A dermoscopy image of a single skin lesion:
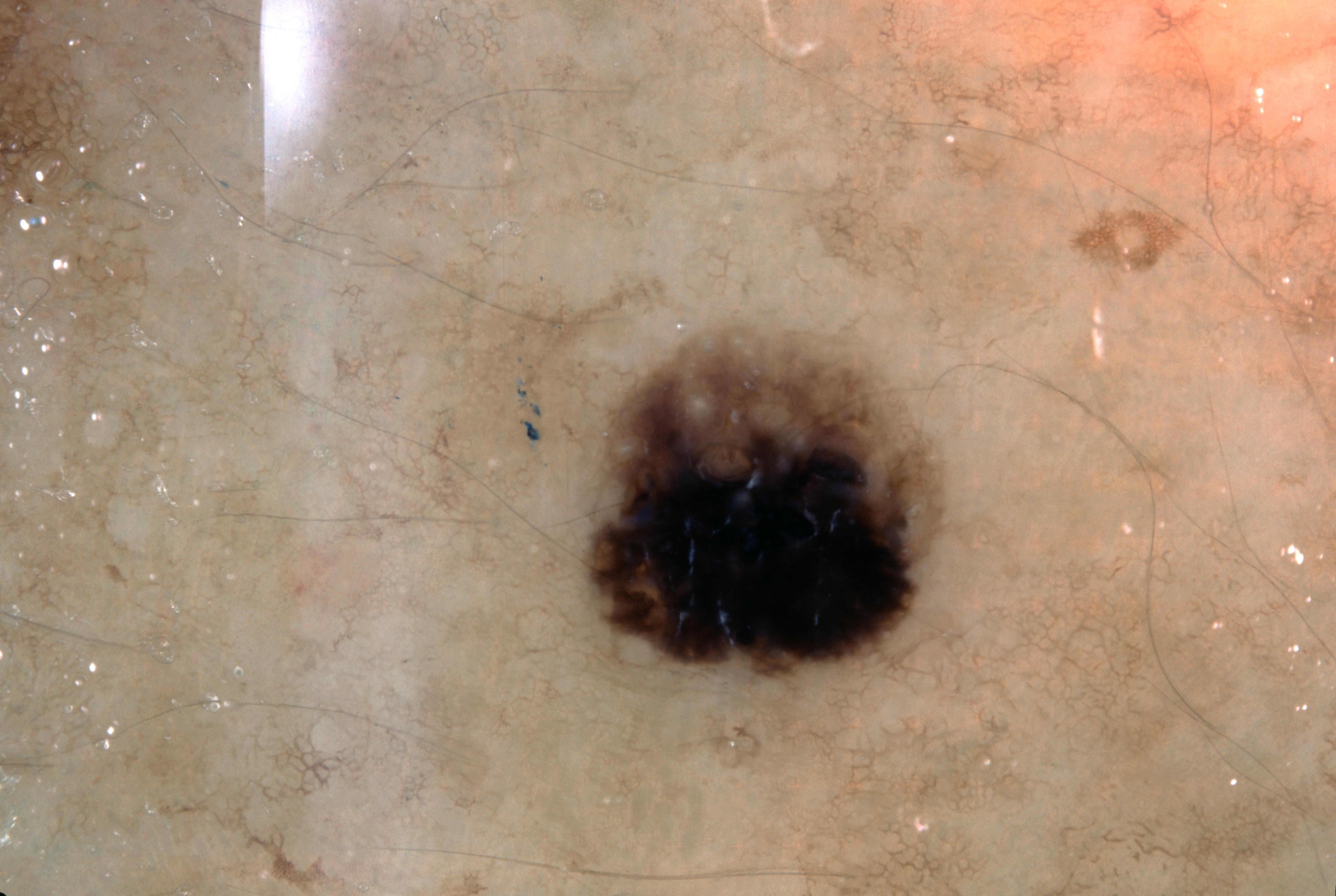Image and clinical context: In (x1, y1, x2, y2) order, the lesion occupies the region <bbox>585, 336, 939, 686</bbox>. The lesion takes up a moderate portion of the field. Dermoscopically, the lesion shows milia-like cysts, pigment network, and streaks, with no negative network. Conclusion: Expert review diagnosed this as a seborrheic keratosis.